Dermoscopy of a skin lesion:
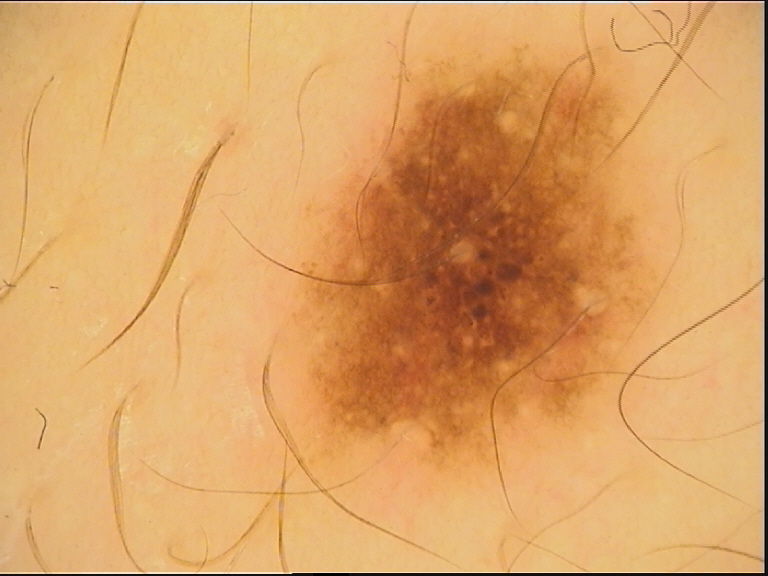diagnosis: dysplastic junctional nevus (expert consensus).